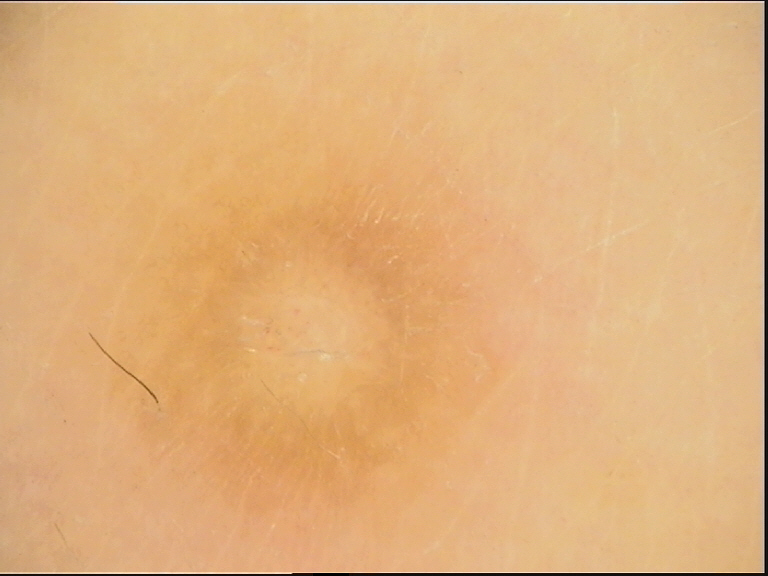<lesion>
<image>dermatoscopy</image>
<lesion_type>
<main_class>fibro-histiocytic</main_class>
</lesion_type>
<diagnosis>
<name>dermatofibroma</name>
<code>df</code>
<malignancy>benign</malignancy>
<super_class>non-melanocytic</super_class>
<confirmation>expert consensus</confirmation>
</diagnosis>
</lesion>